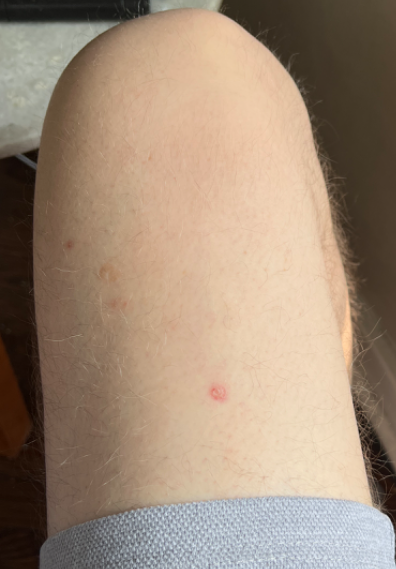{
  "body_site": "leg",
  "patient": "male, age 60–69",
  "shot_type": "at a distance",
  "differential": {
    "tied_lead": [
      "Basal Cell Carcinoma",
      "SCC/SCCIS",
      "Skin cancer",
      "Psoriasis",
      "Inflicted skin lesions"
    ],
    "unlikely": [
      "Eczema"
    ]
  }
}